A dermoscopy image of a single skin lesion; a male patient, aged approximately 55: 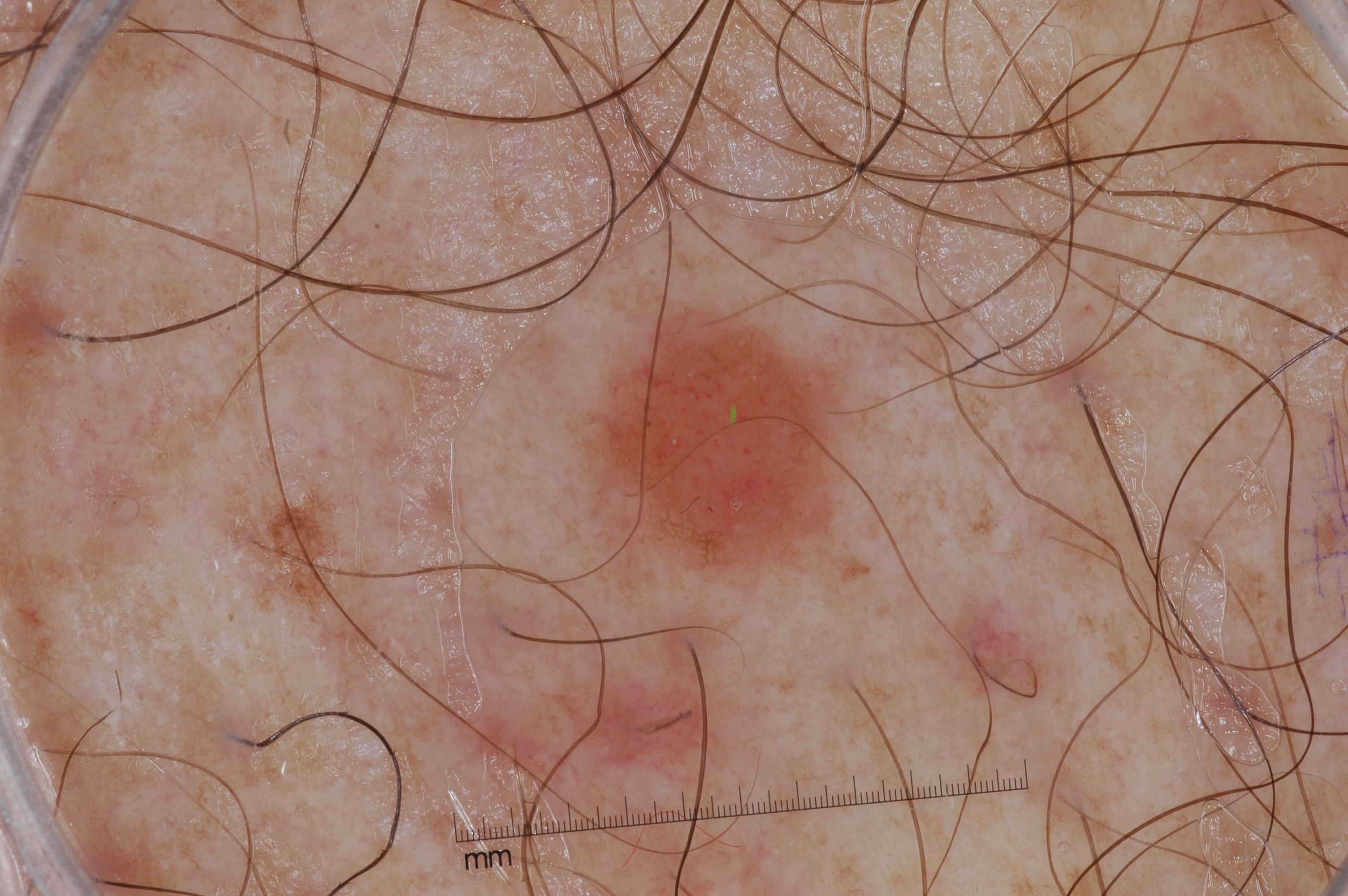Q: What is the lesion's bounding box?
A: x1=590, y1=315, x2=842, y2=567
Q: What dermoscopic features are present?
A: pigment network and milia-like cysts
Q: What did the assessment conclude?
A: a melanocytic nevus, a benign lesion